The photograph was taken at an angle:
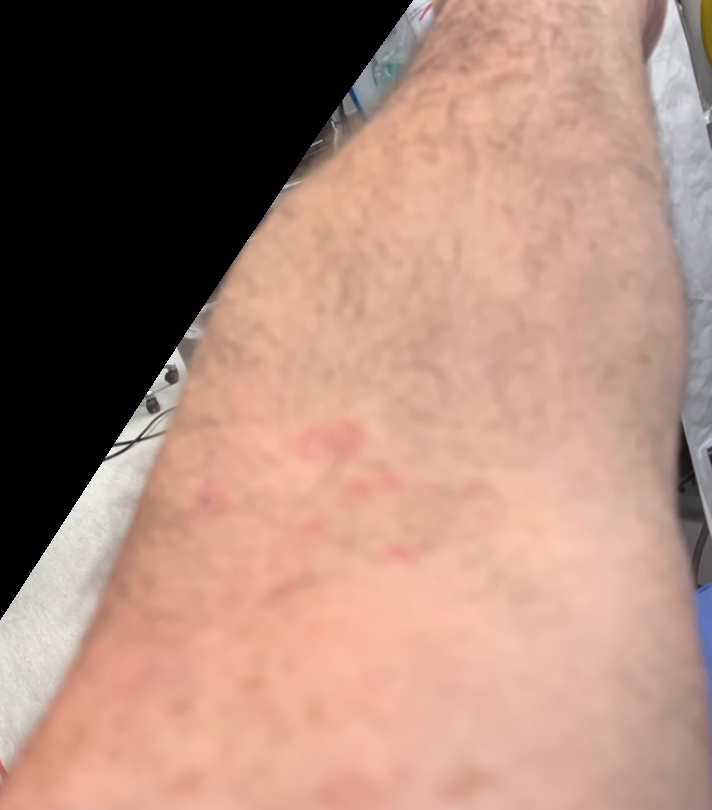differential:
  tied_lead:
    - Herpes Zoster
    - Allergic Contact Dermatitis